A dermoscopy image of a single skin lesion:
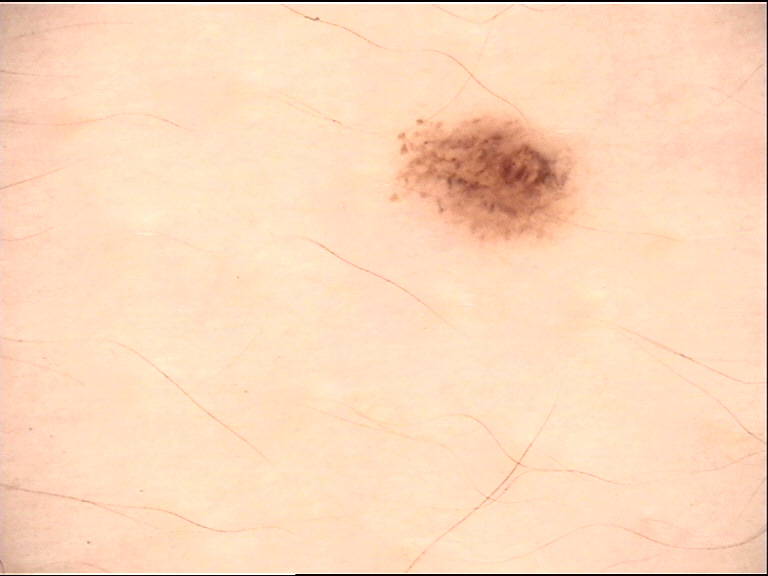The morphology is that of a banal lesion.
Consistent with a compound nevus.